Located on the arm and leg, this is a close-up image — 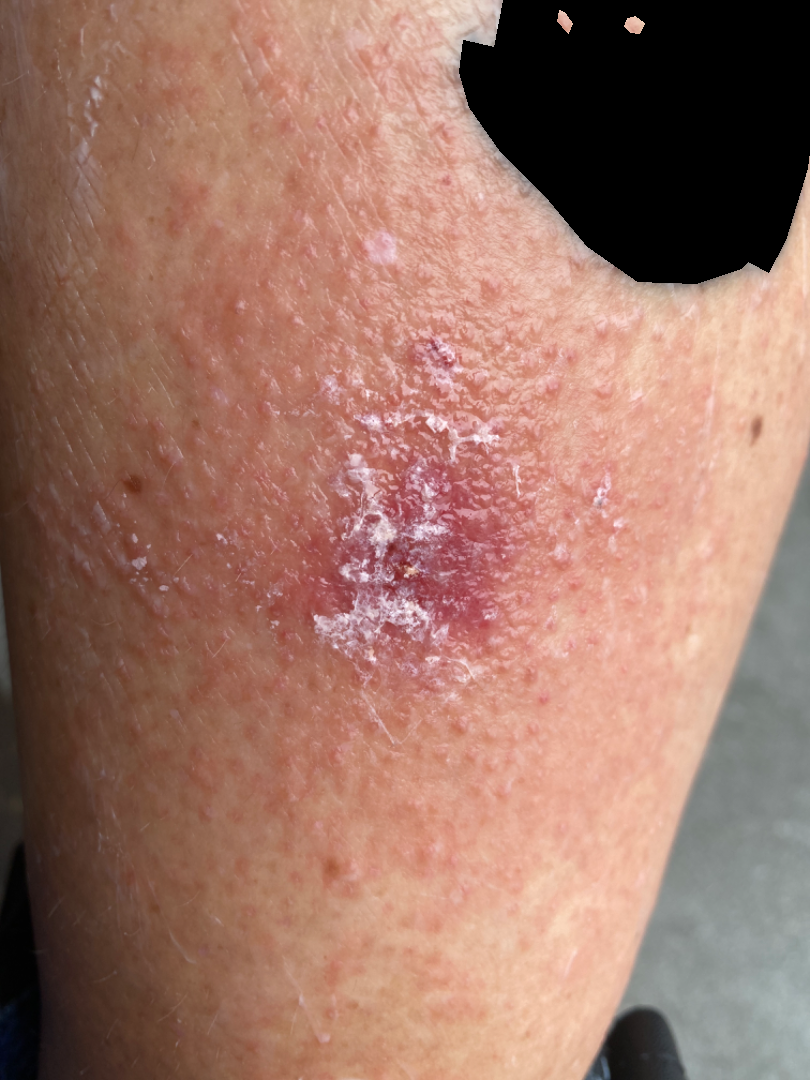One reviewing dermatologist: the differential, in no particular order, includes Impetigo and Allergic Contact Dermatitis.